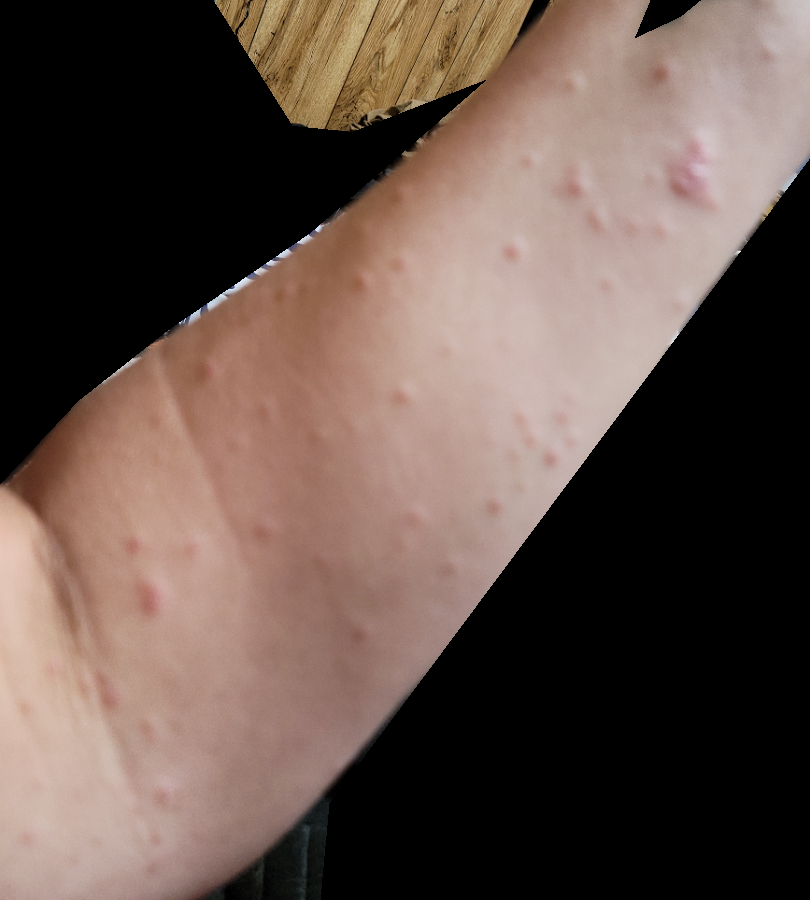The reviewing panel's impression was: the leading consideration is Psoriasis; also consider Lichen planus/lichenoid eruption; lower on the differential is Scabies; less probable is Lymphomatoid papulosis; less likely is Pityriasis lichenoides.